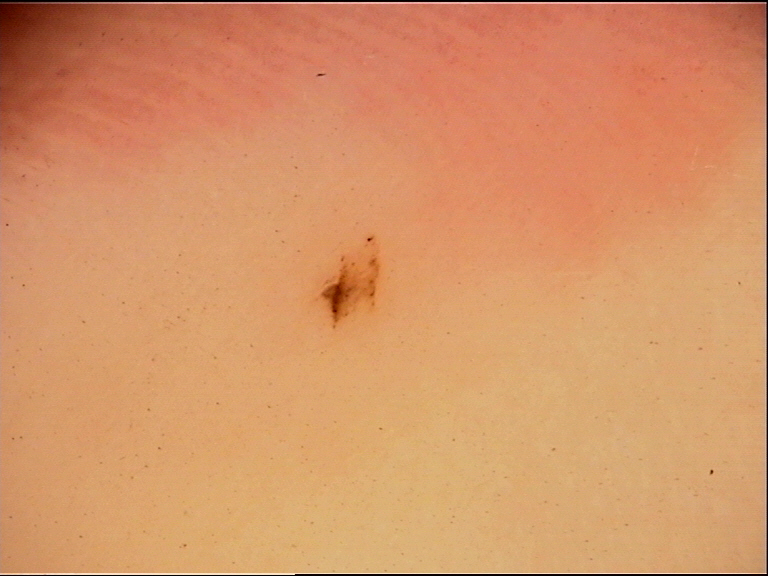class = acral junctional nevus (expert consensus)